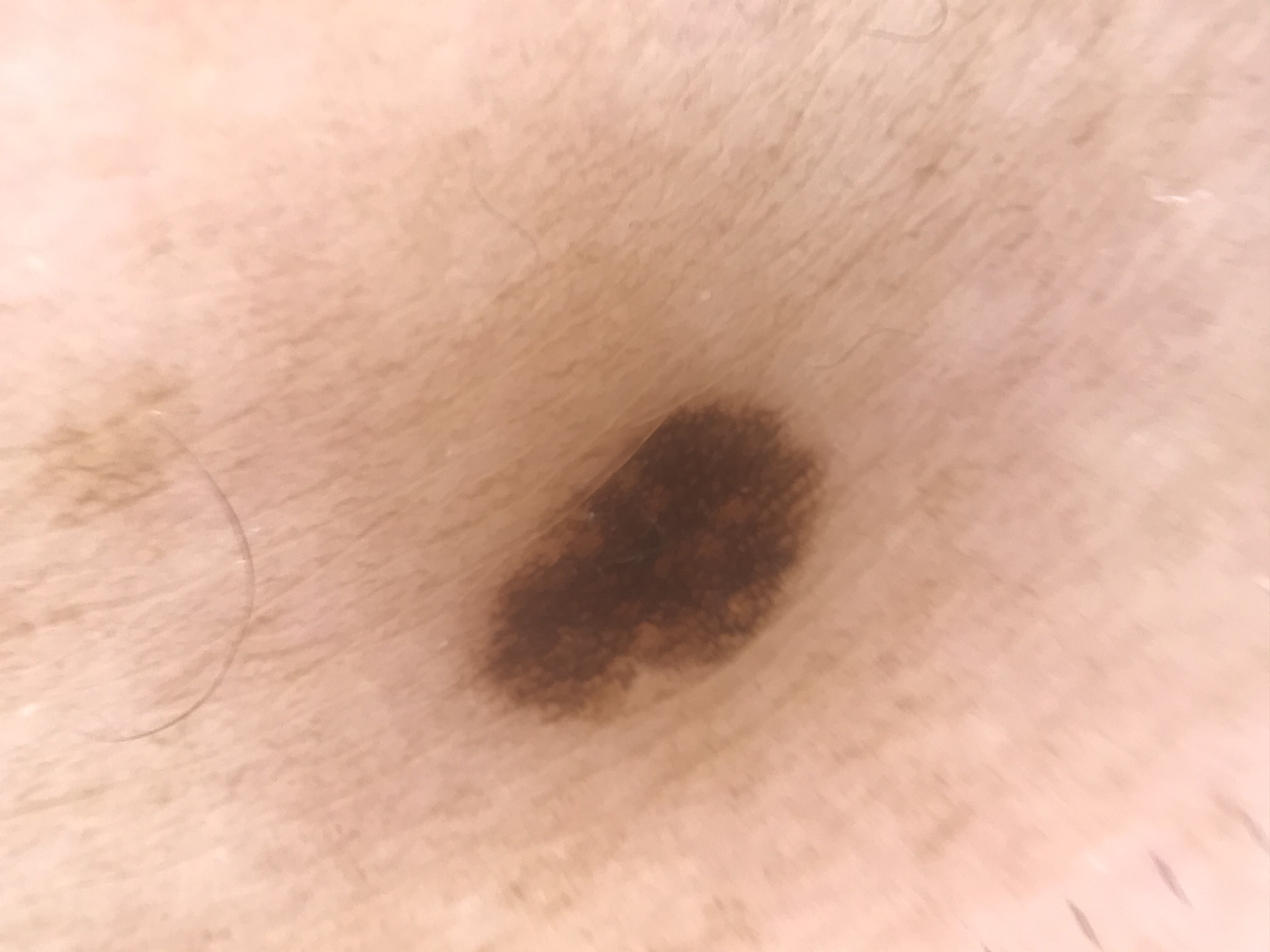A dermoscopic close-up of a skin lesion.
Labeled as a benign lesion — a dysplastic junctional nevus.